A dermoscopic close-up of a skin lesion.
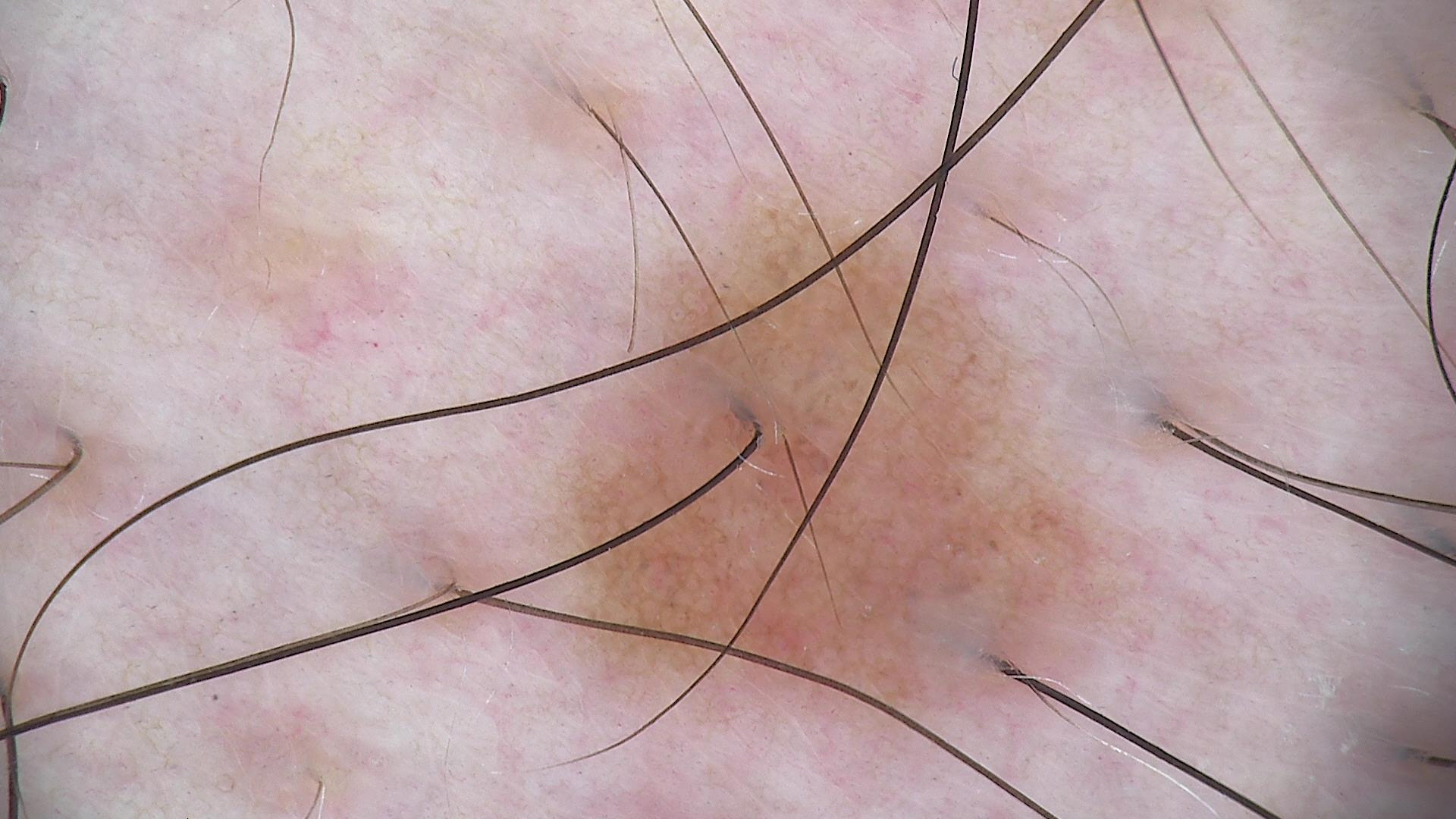The diagnostic label was a benign lesion — a dysplastic junctional nevus.